A dermoscopic view of a skin lesion:
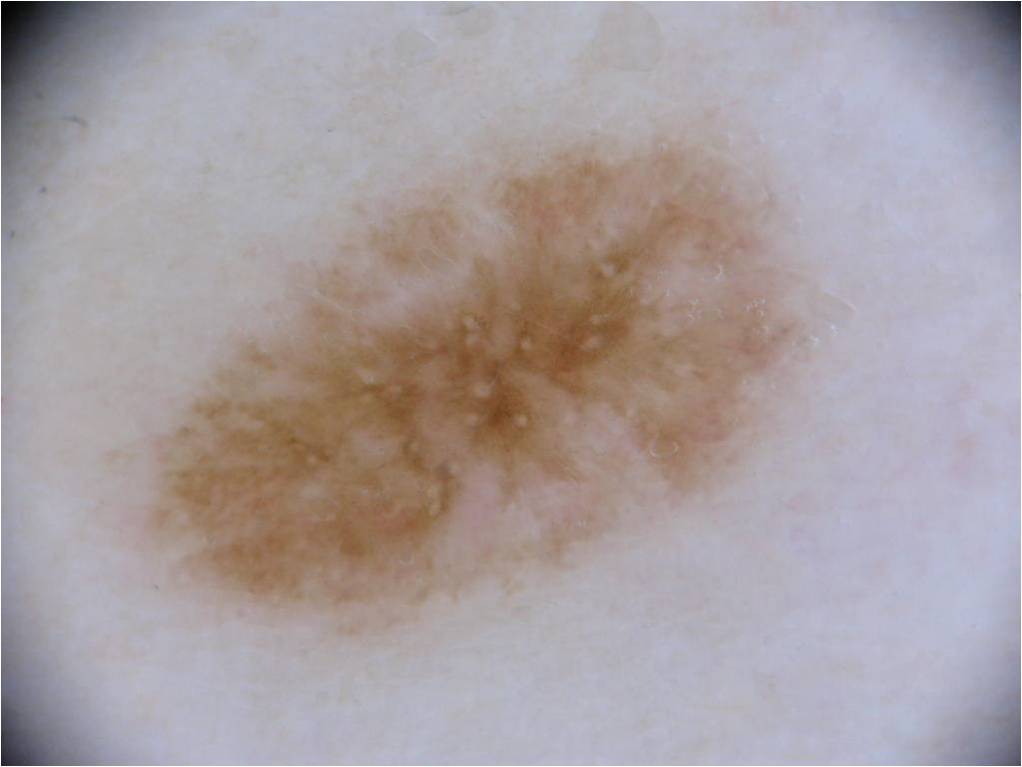Findings:
As (left, top, right, bottom), the lesion occupies the region (142, 136, 800, 637).
Conclusion:
Consistent with a melanocytic nevus, a benign lesion.